The photo was captured at an angle; located on the back of the hand; female patient, age 30–39 — 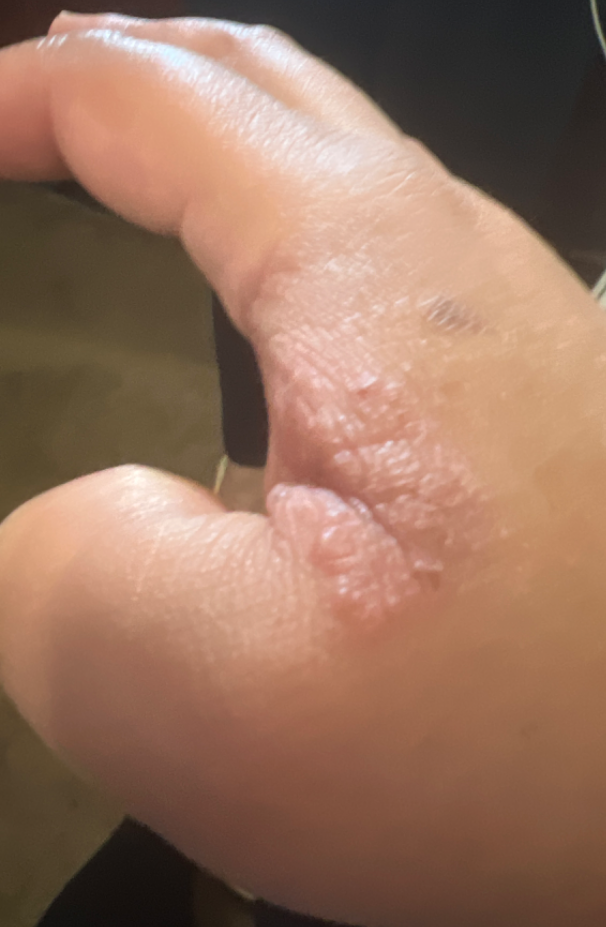Review:
The reviewing panel's impression was: Candida (considered); Eczema (considered); Tinea (less likely); Psoriasis (less likely).